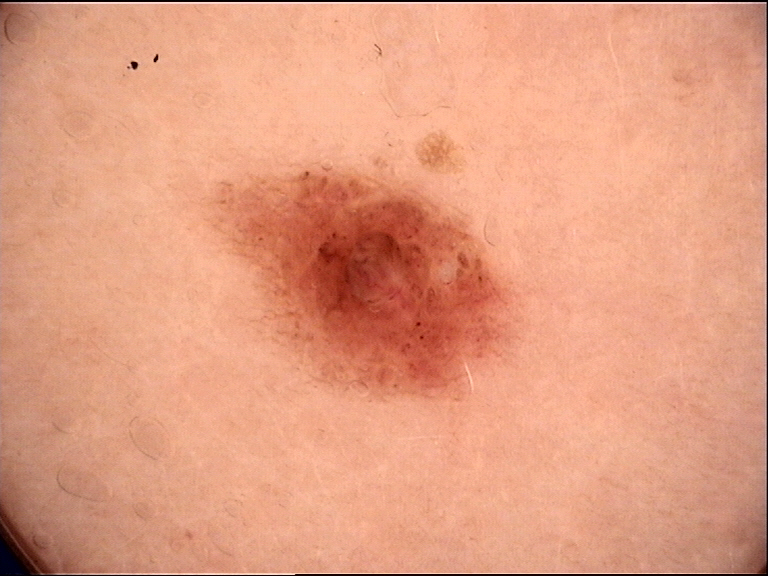– modality · dermatoscopy
– class · dysplastic compound nevus (expert consensus)